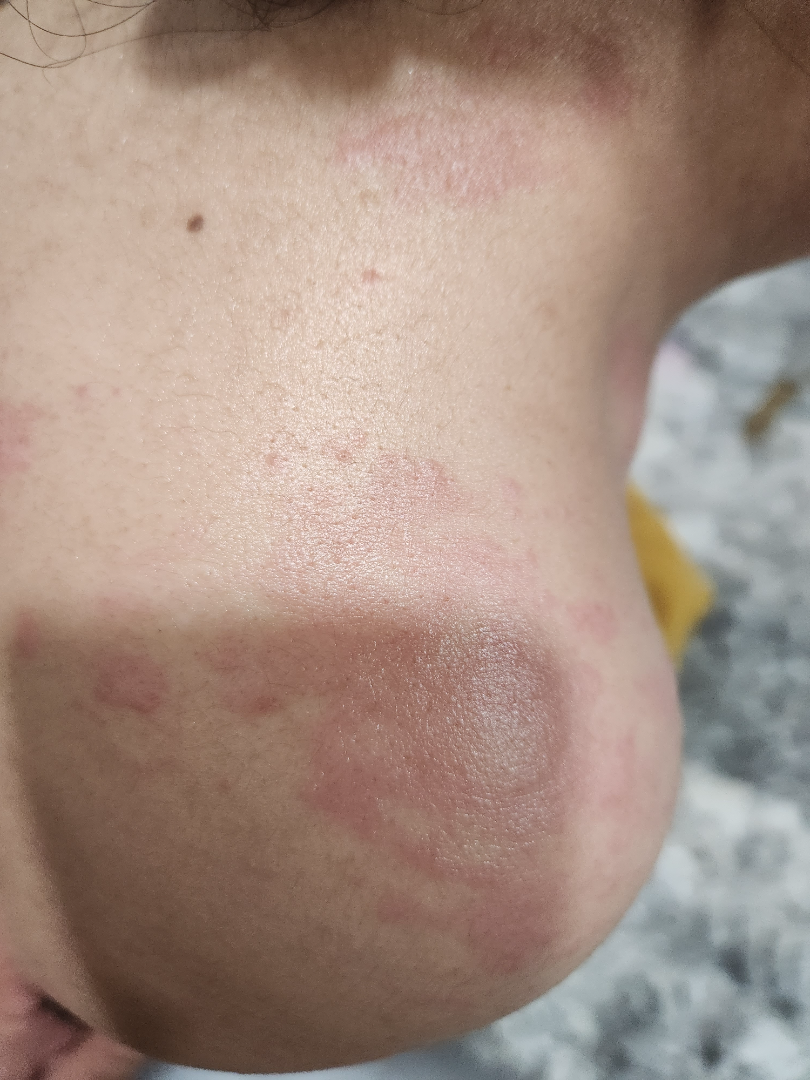Impression:
On photographic review, Allergic Contact Dermatitis (weight 0.67); Herpes Zoster (weight 0.33).